A dermoscopic photograph of a skin lesion.
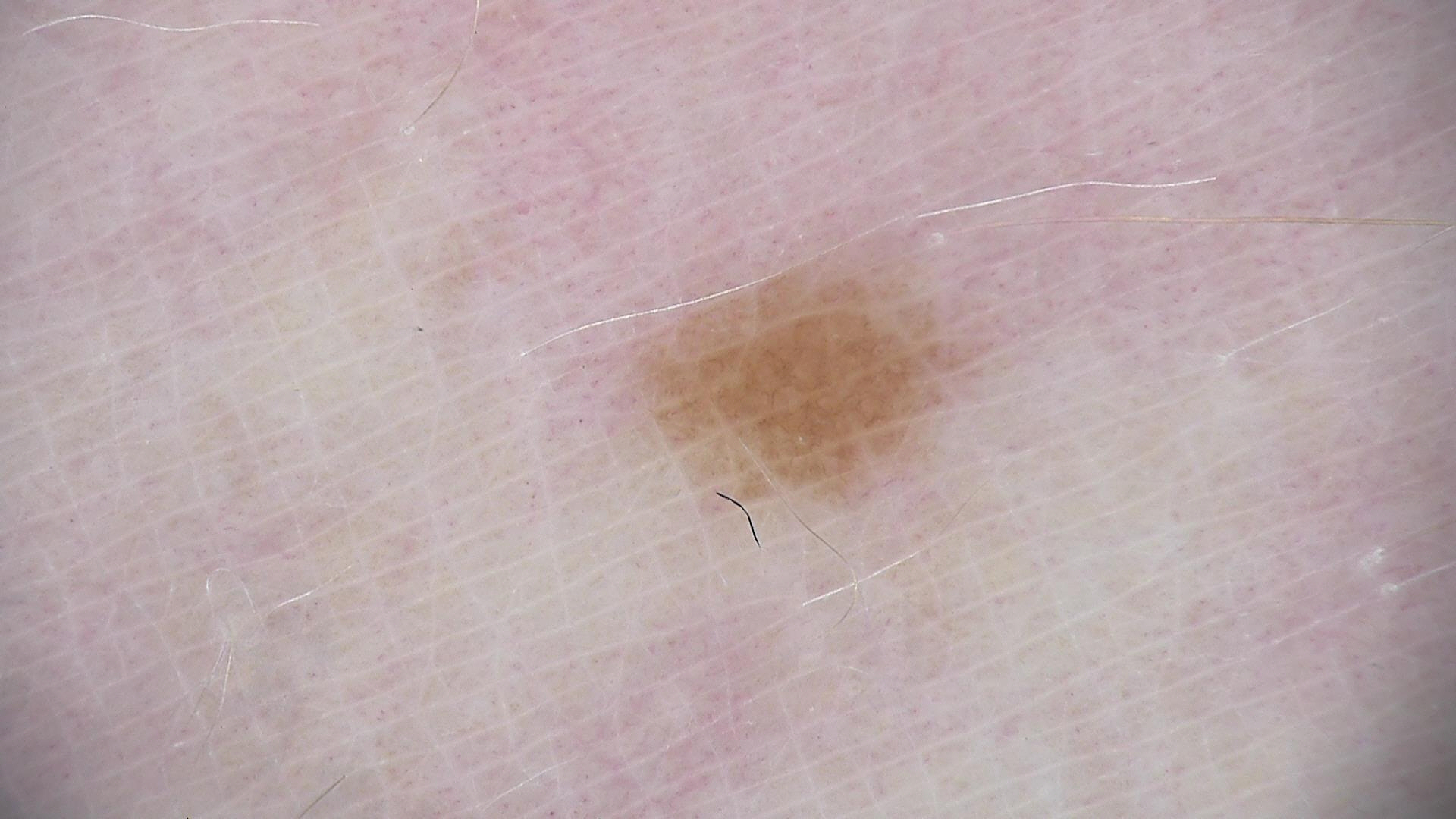lesion type=banal
label=junctional nevus (expert consensus)